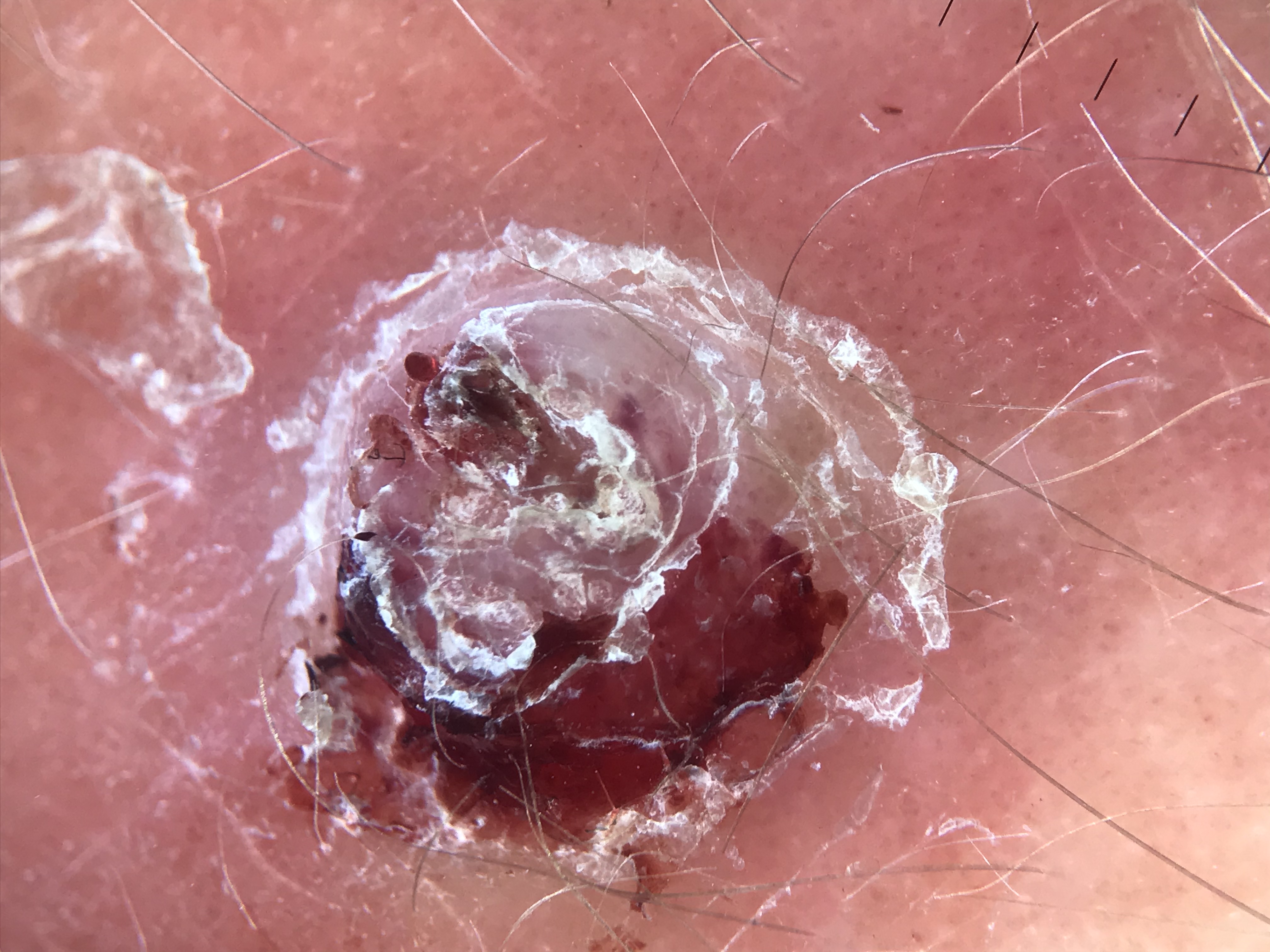A dermoscopic close-up of a skin lesion. This is a keratinocytic lesion. Biopsy-confirmed as a malignancy — a squamous cell carcinoma.